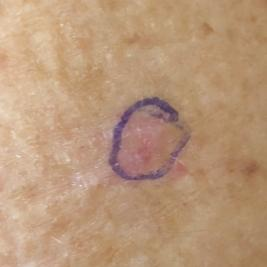subject: female, in their 70s
imaging: clinical photo
anatomic site: a forearm
reported symptoms: elevation, itching / no pain, no growth
assessment: actinic keratosis (clinical consensus)